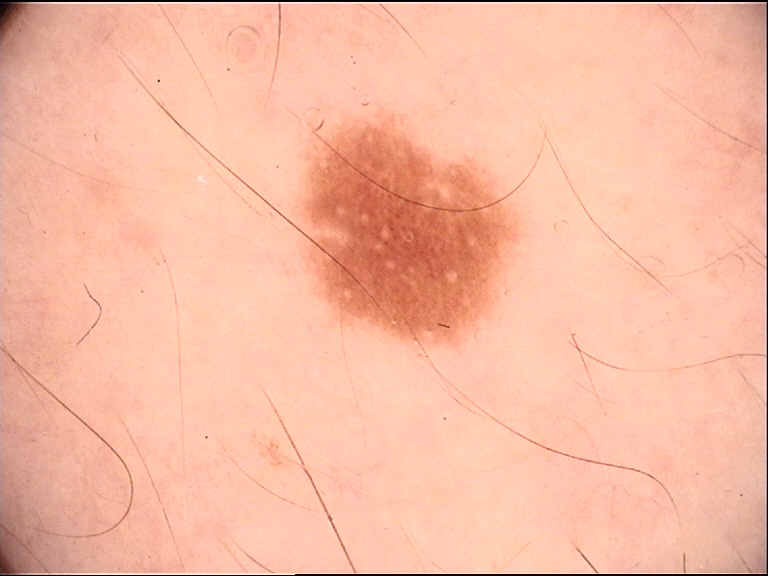Labeled as a dysplastic junctional nevus.